Close-up view — 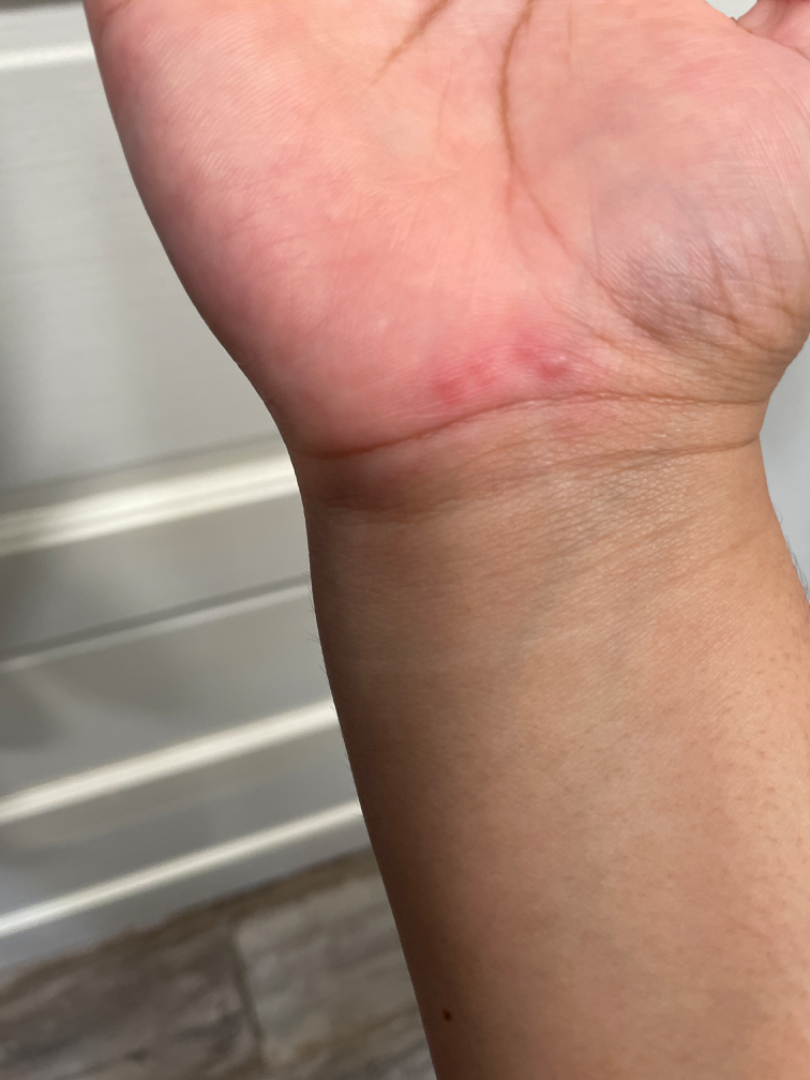On dermatologist assessment of the image, most likely Viral Exanthem; the differential also includes Herpes Simplex.